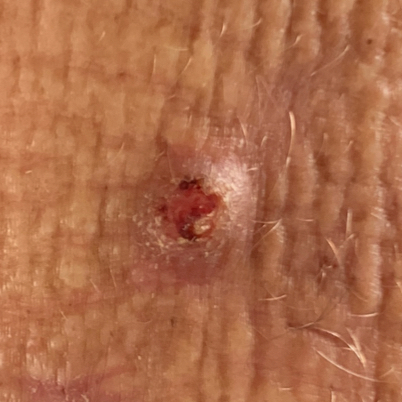Pathology: The biopsy diagnosis was a squamous cell carcinoma.